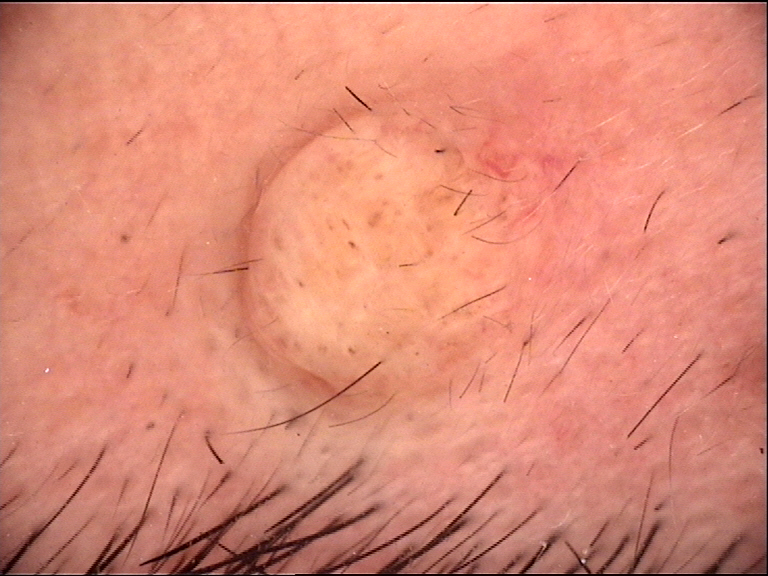A dermoscopic image of a skin lesion. The morphology is that of a banal lesion. The diagnostic label was a dermal nevus.